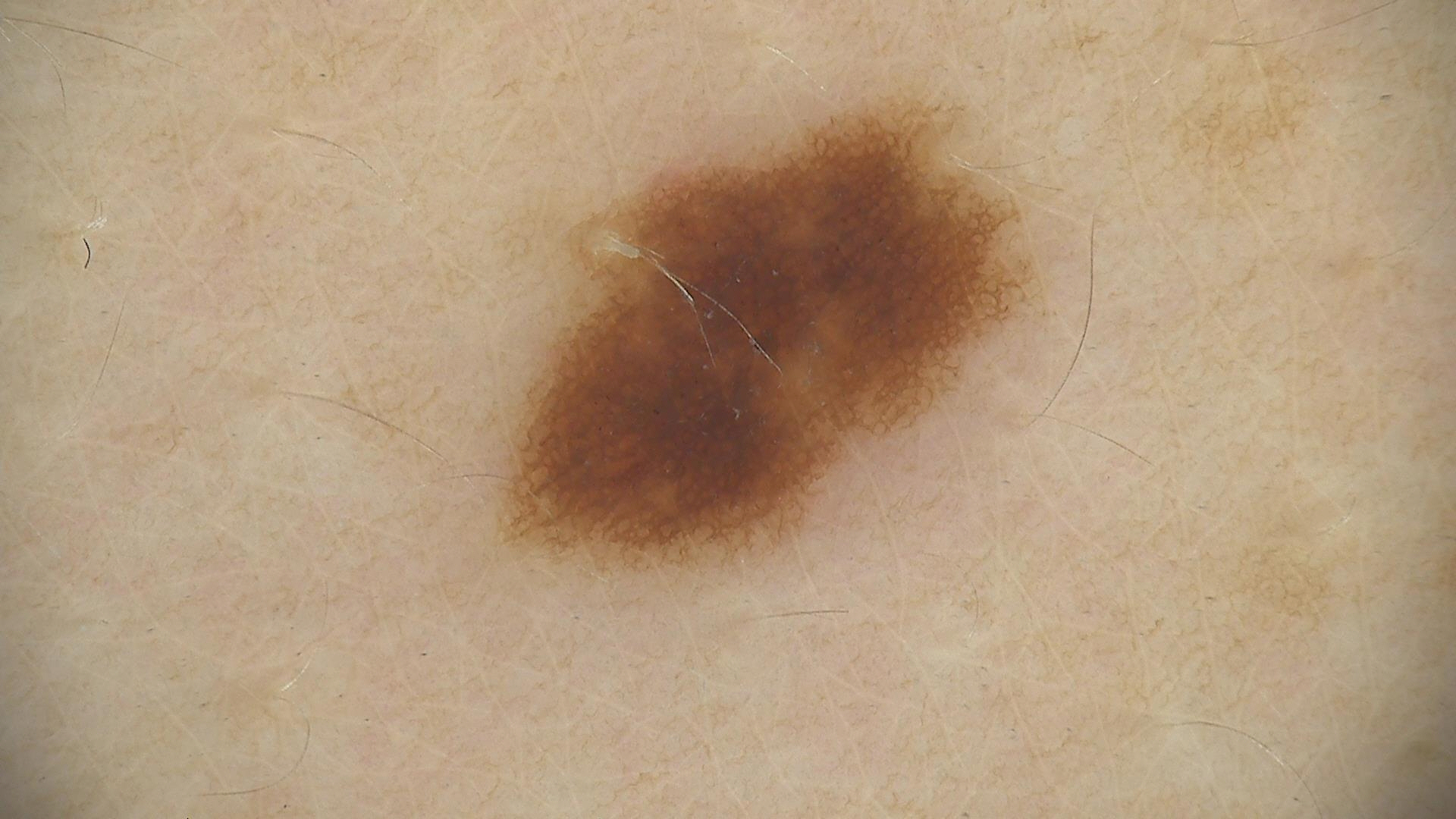Labeled as a dysplastic junctional nevus.